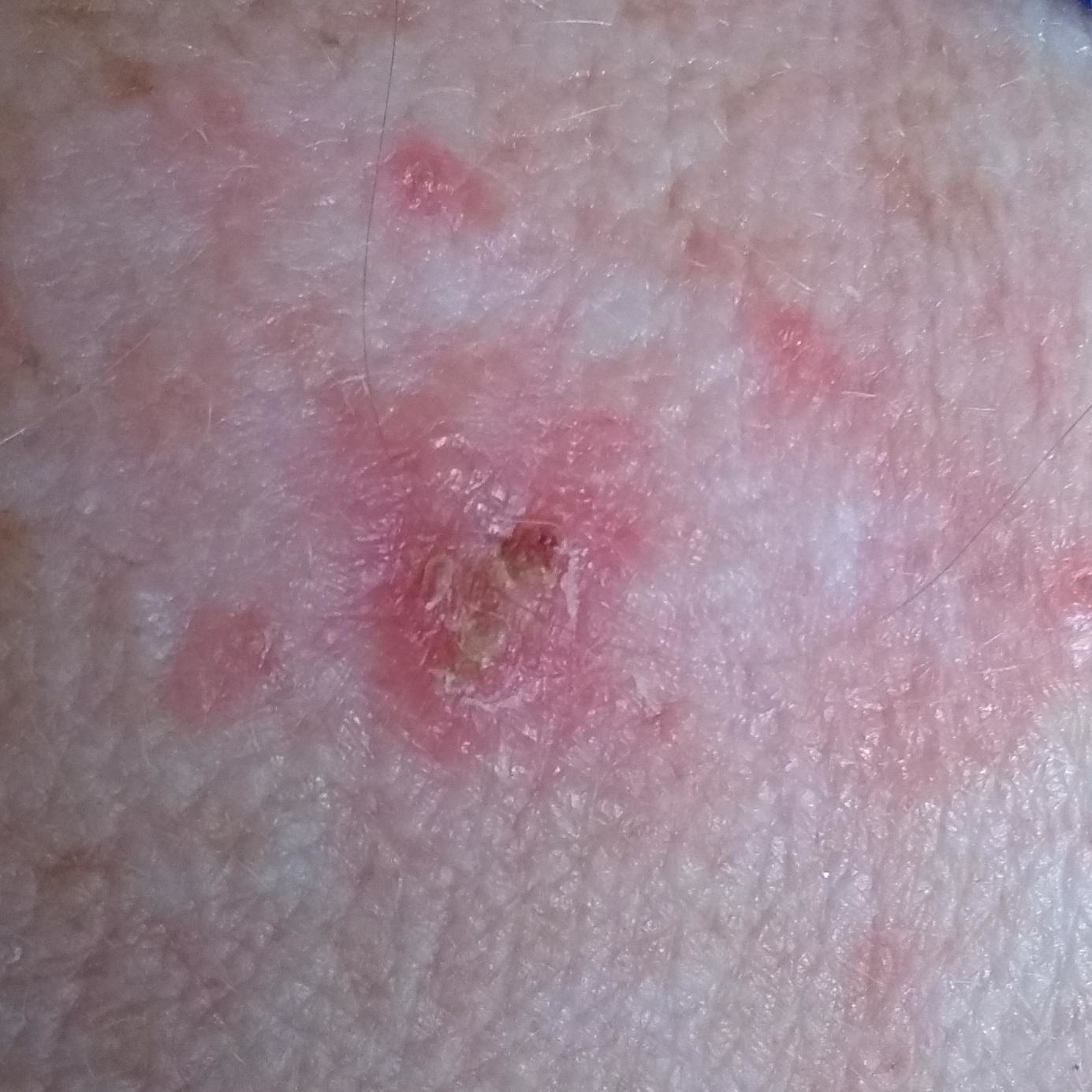Histopathologically confirmed as a basal cell carcinoma.